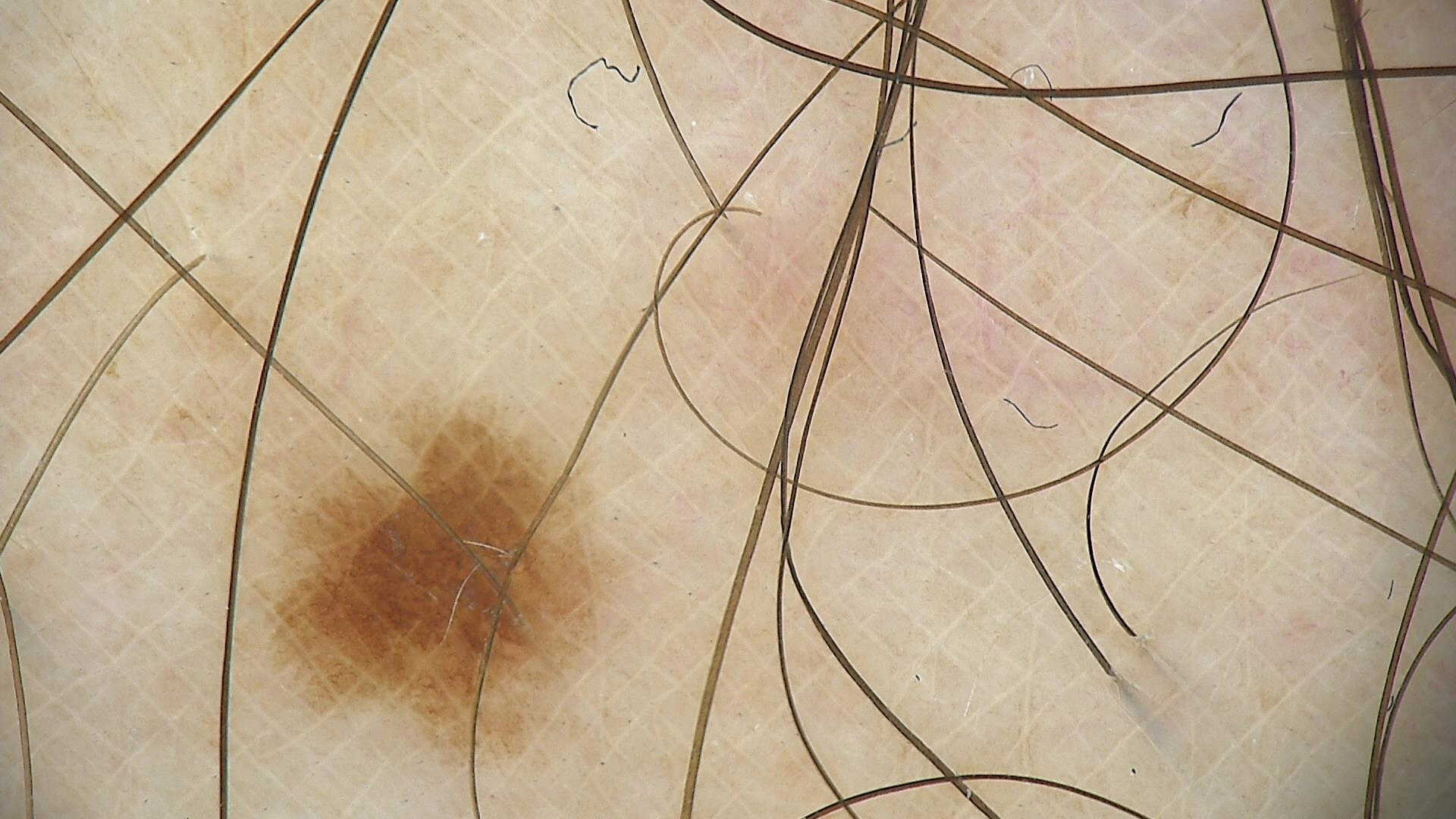The diagnosis was a banal lesion — a junctional nevus.